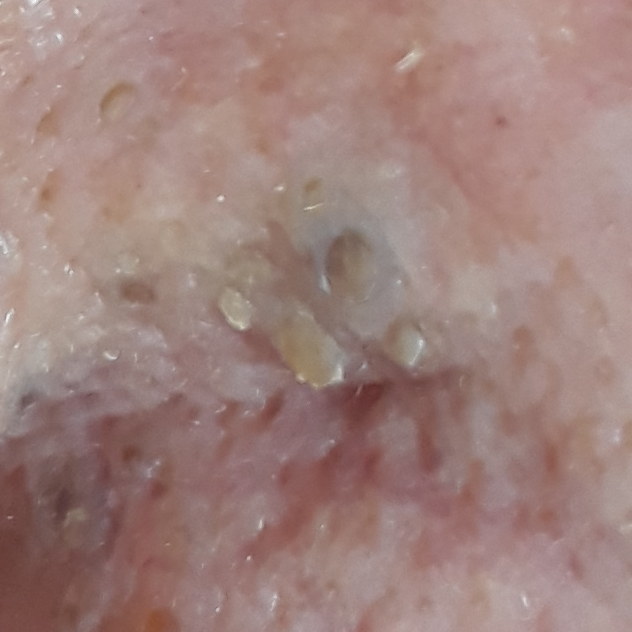A clinical close-up photograph of a skin lesion. A subject in their 80s. By the patient's account, the lesion is elevated and itches. The consensus clinical diagnosis was a seborrheic keratosis.